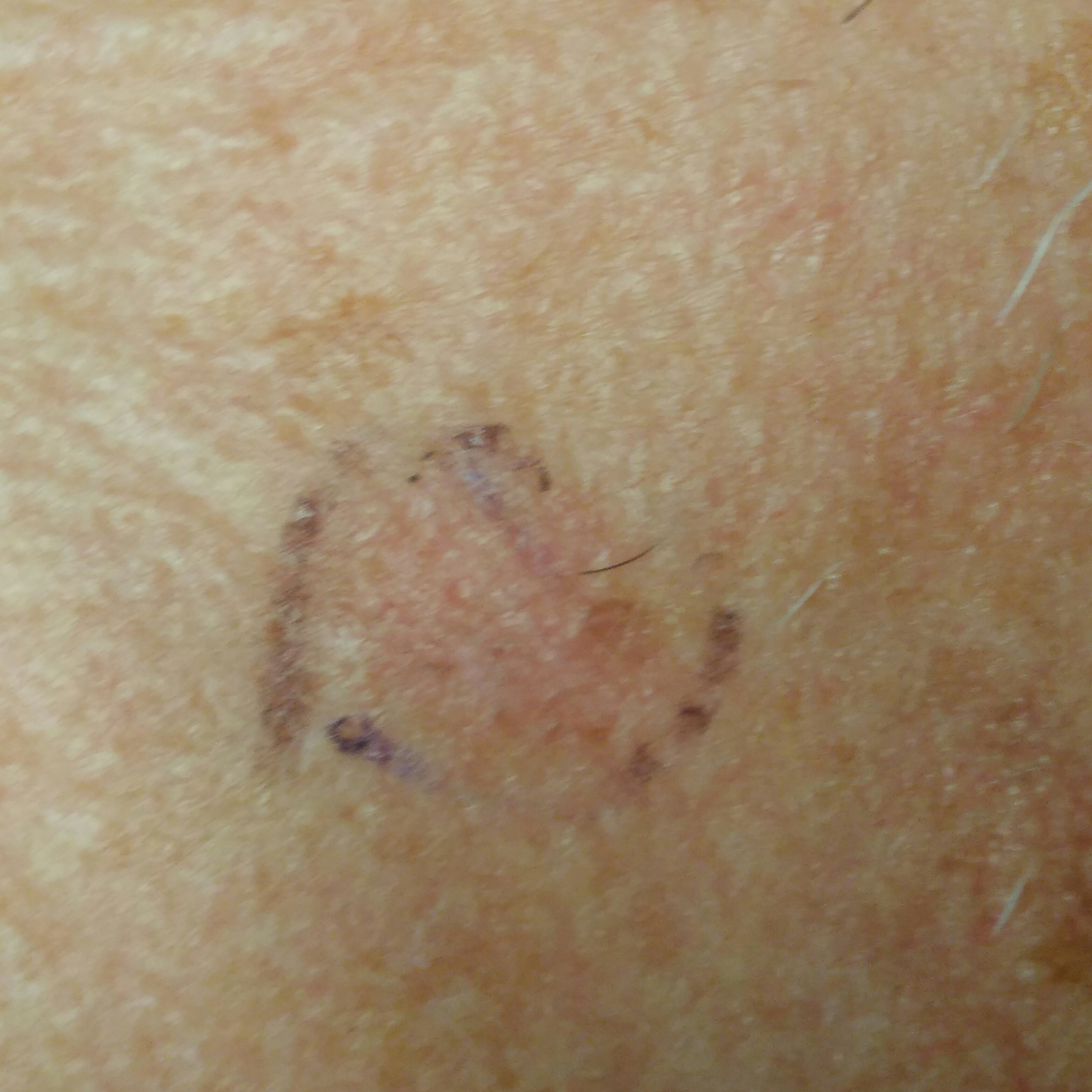Q: Who is the patient?
A: in their 50s
Q: How was this image acquired?
A: clinical photograph
Q: What is the anatomic site?
A: the face
Q: What does the patient describe?
A: itching, growth, elevation / no pain, no bleeding
Q: What is this lesion?
A: actinic keratosis (clinical consensus)